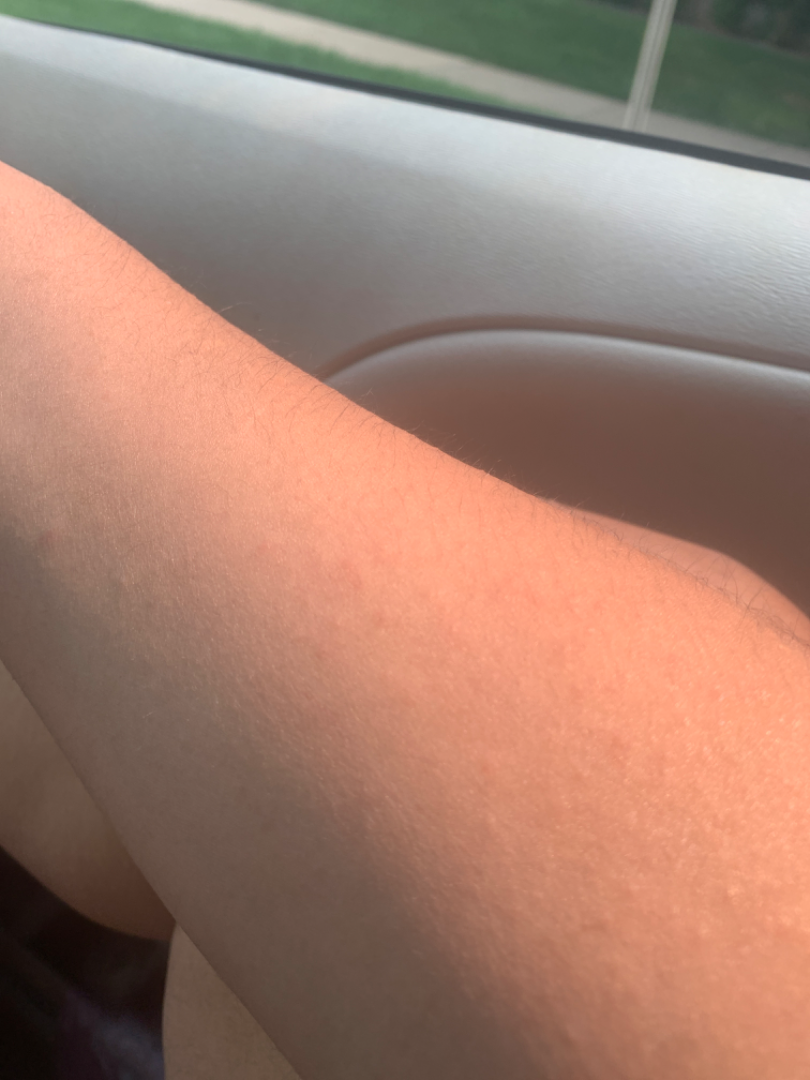Assessment: On teledermatology review, most consistent with Keratosis pilaris.